An image taken at a distance, the subject is a male aged 18–29, the front of the torso is involved:
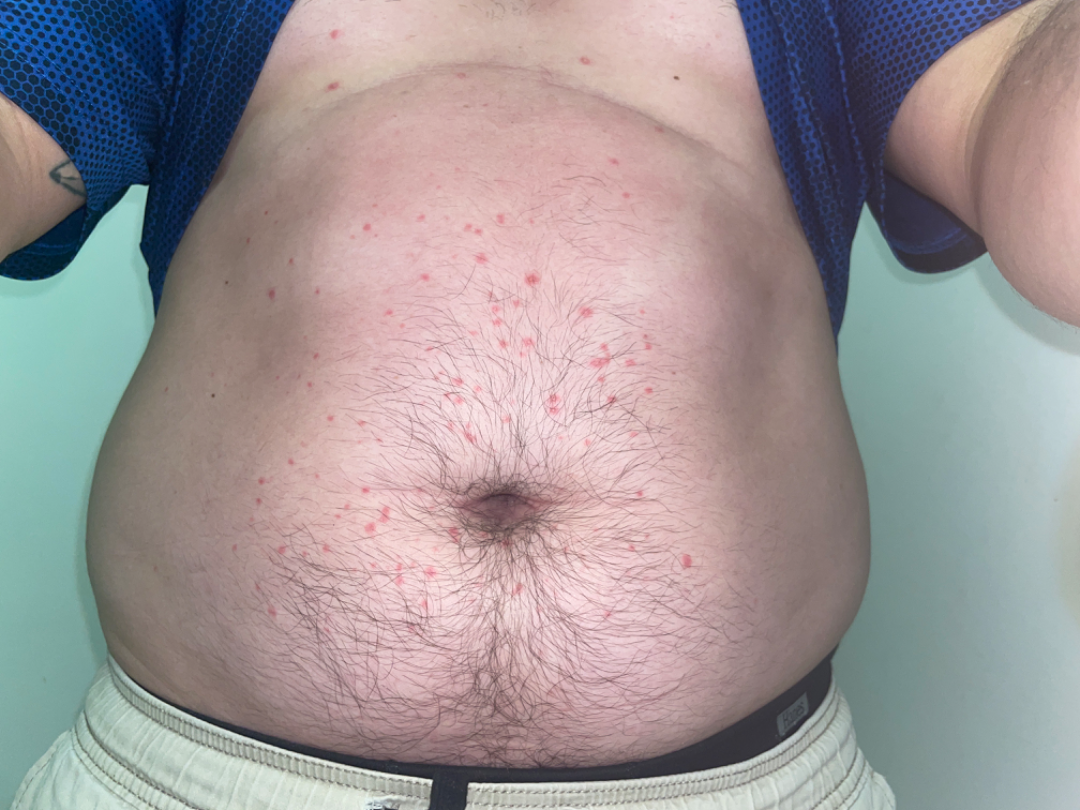<case>
  <assessment>not assessable</assessment>
  <texture>raised or bumpy, fluid-filled</texture>
  <duration>less than one week</duration>
  <symptoms>bothersome appearance</symptoms>
  <patient_category>a rash</patient_category>
</case>